A dermoscopic photograph of a skin lesion.
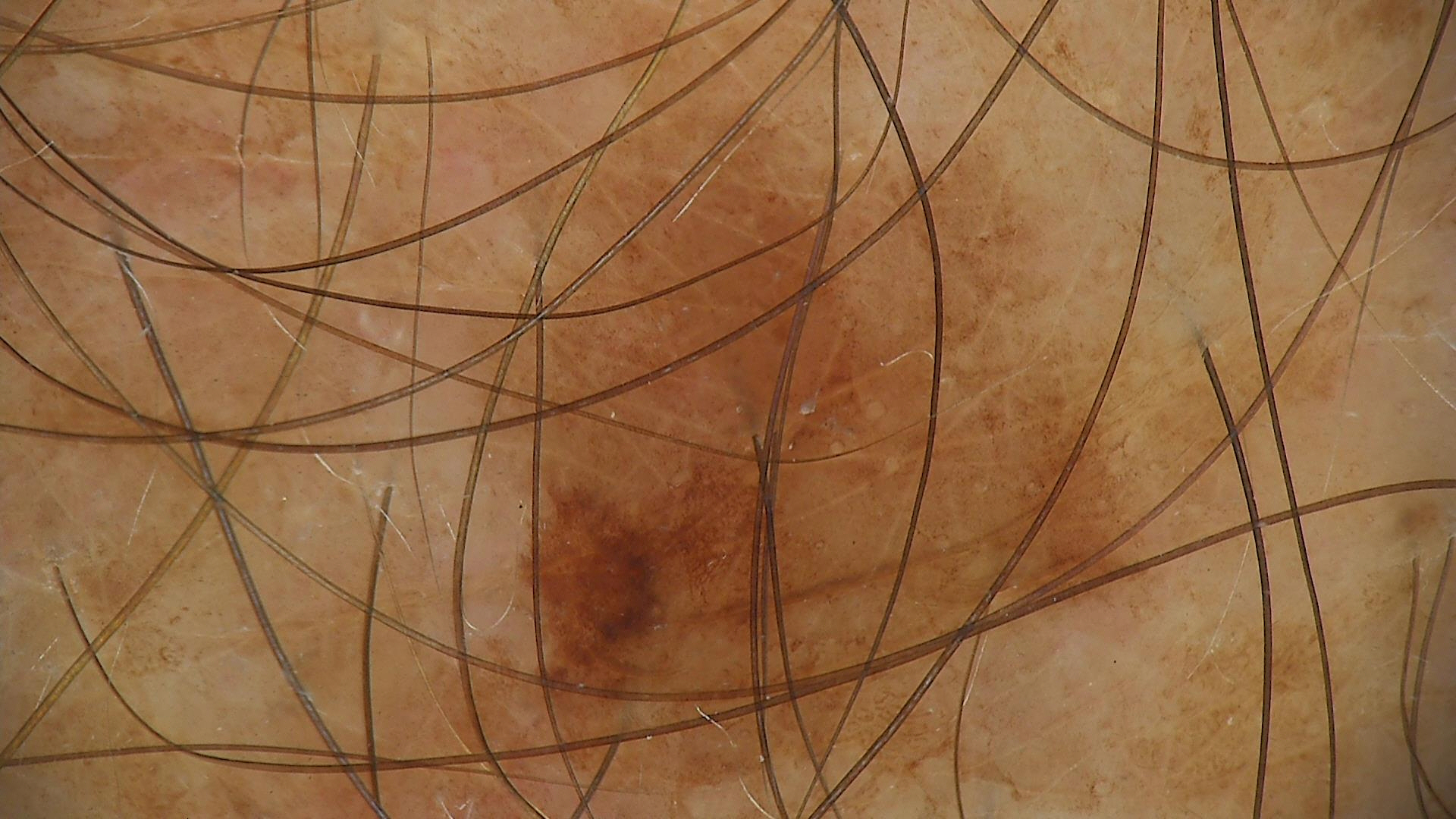Consistent with a solar lentigo.